The affected area is the head or neck. The patient is a female aged 18–29. Skin tone: FST V; non-clinician graders estimated Monk skin tone scale 6 (US pool) or 5 (India pool). The condition has been present for less than one week. The patient notes the lesion is raised or bumpy. Symptoms reported: bothersome appearance and enlargement. The photograph was taken at an angle.
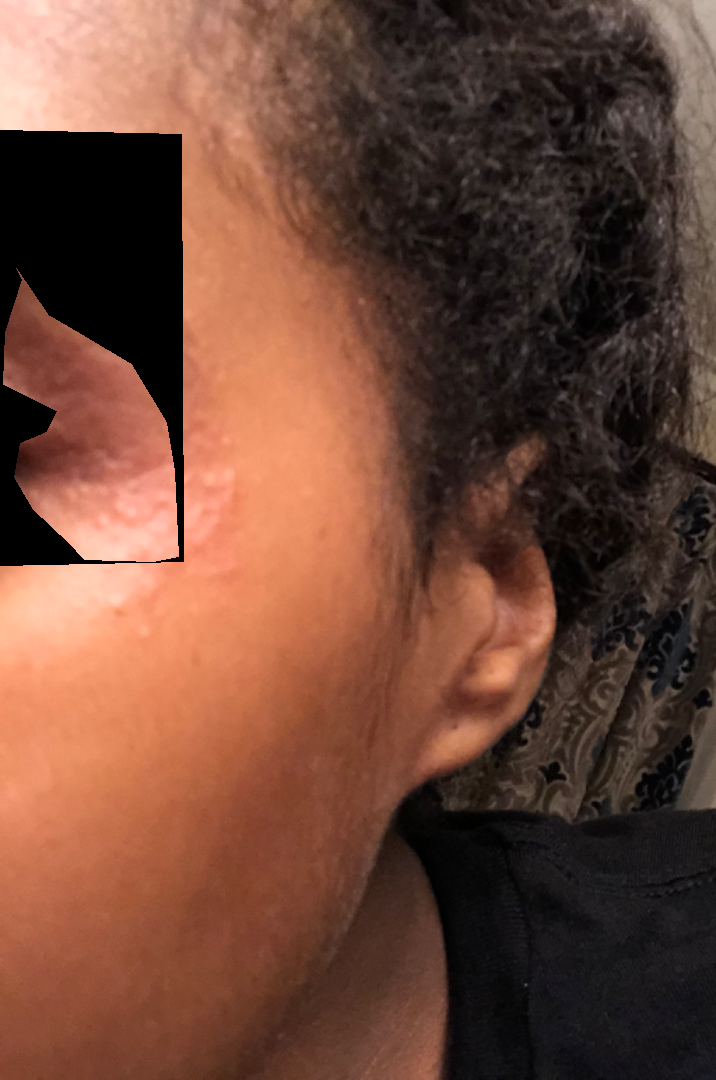Review:
The case was difficult to assess from the available photograph.